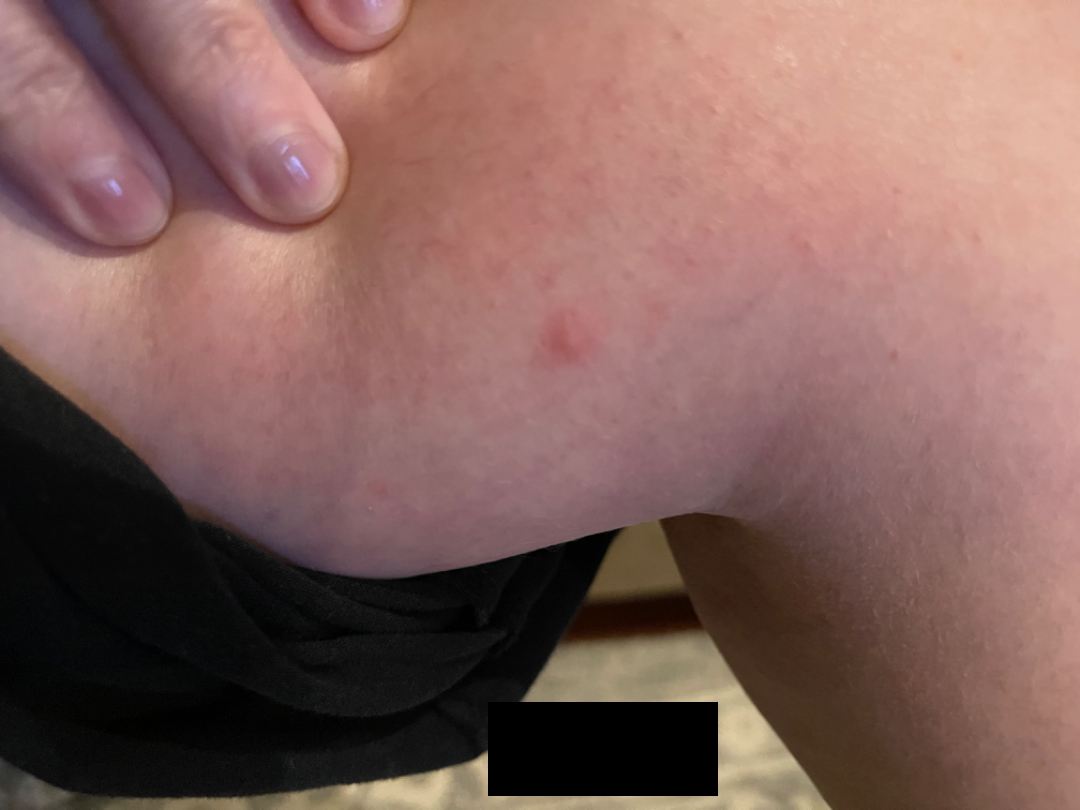Q: What was the assessment?
A: indeterminate from the photograph
Q: How was the photo taken?
A: close-up